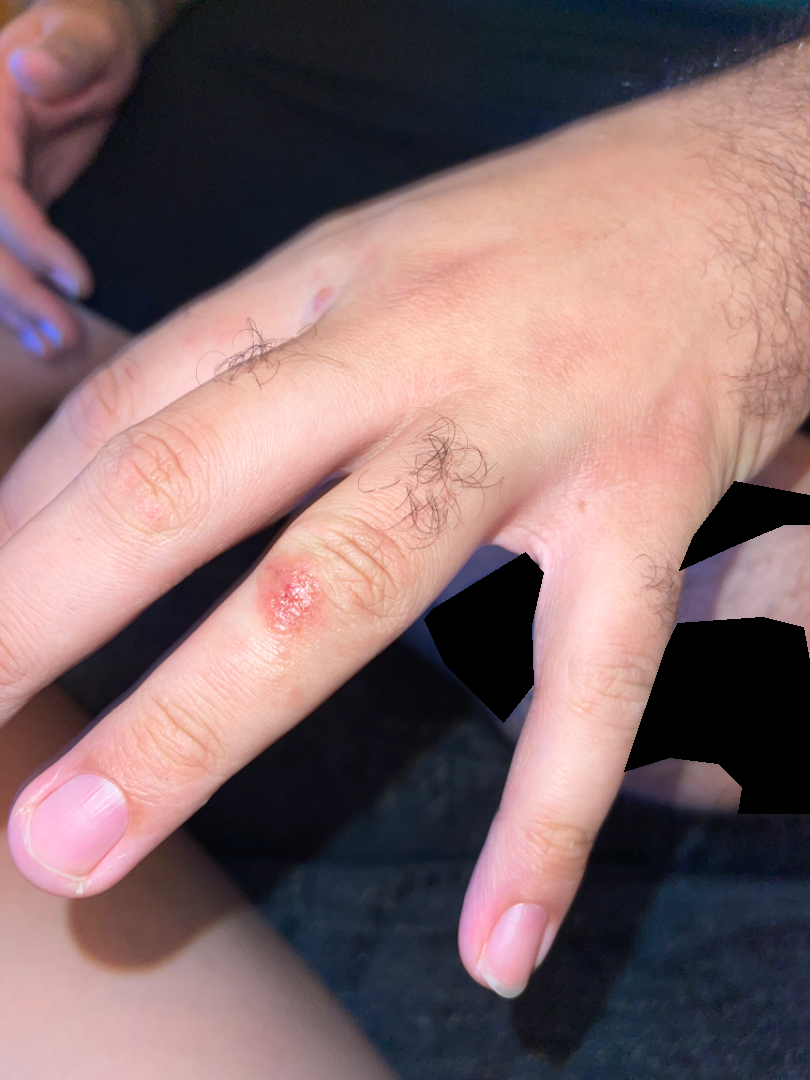{
  "assessment": "ungradable on photographic review",
  "patient_category": "a rash",
  "texture": "raised or bumpy",
  "shot_type": "at an angle",
  "symptoms": [
    "itching",
    "enlargement",
    "pain",
    "bothersome appearance",
    "burning"
  ],
  "duration": "one to four weeks",
  "body_site": [
    "back of the hand",
    "arm",
    "head or neck"
  ]
}